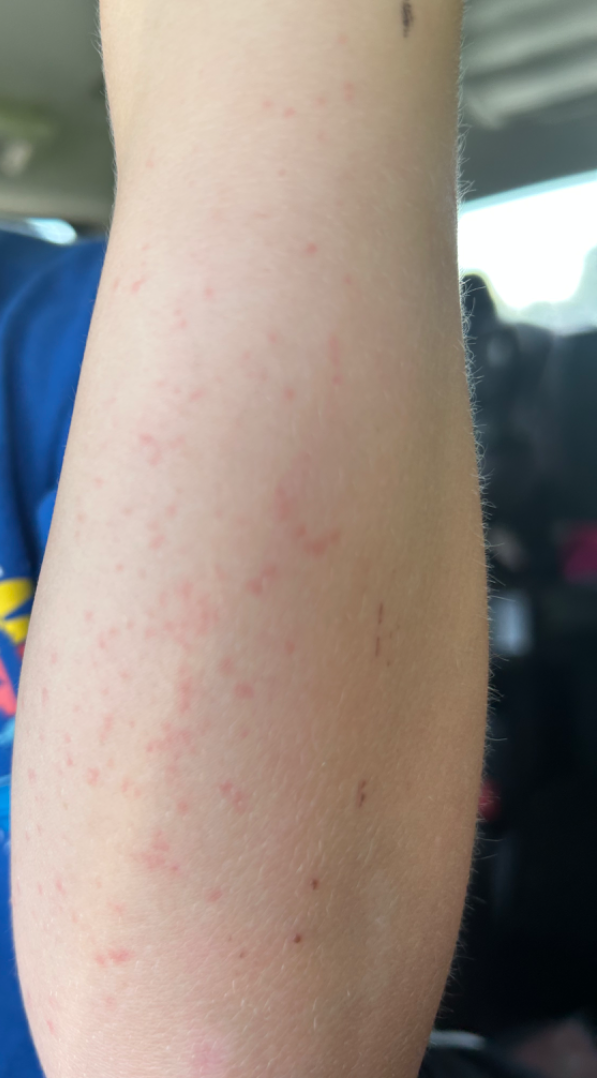The case was difficult to assess from the available photograph.
The photograph is a close-up of the affected area.
The arm is involved.